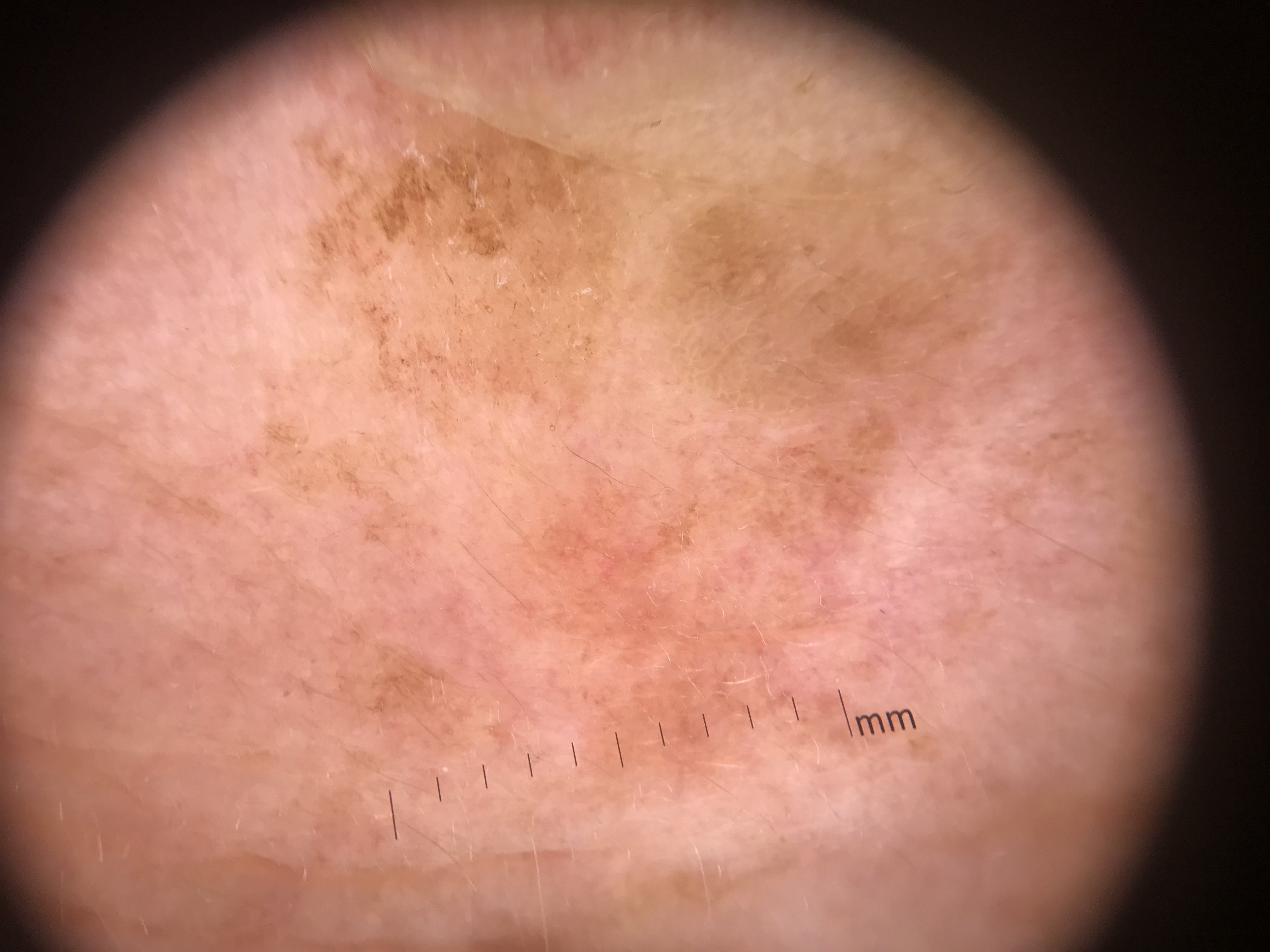subtype = keratinocytic
class = seborrheic keratosis (expert consensus)